Located on the leg and arm. The subject is a male aged 30–39. This image was taken at a distance: 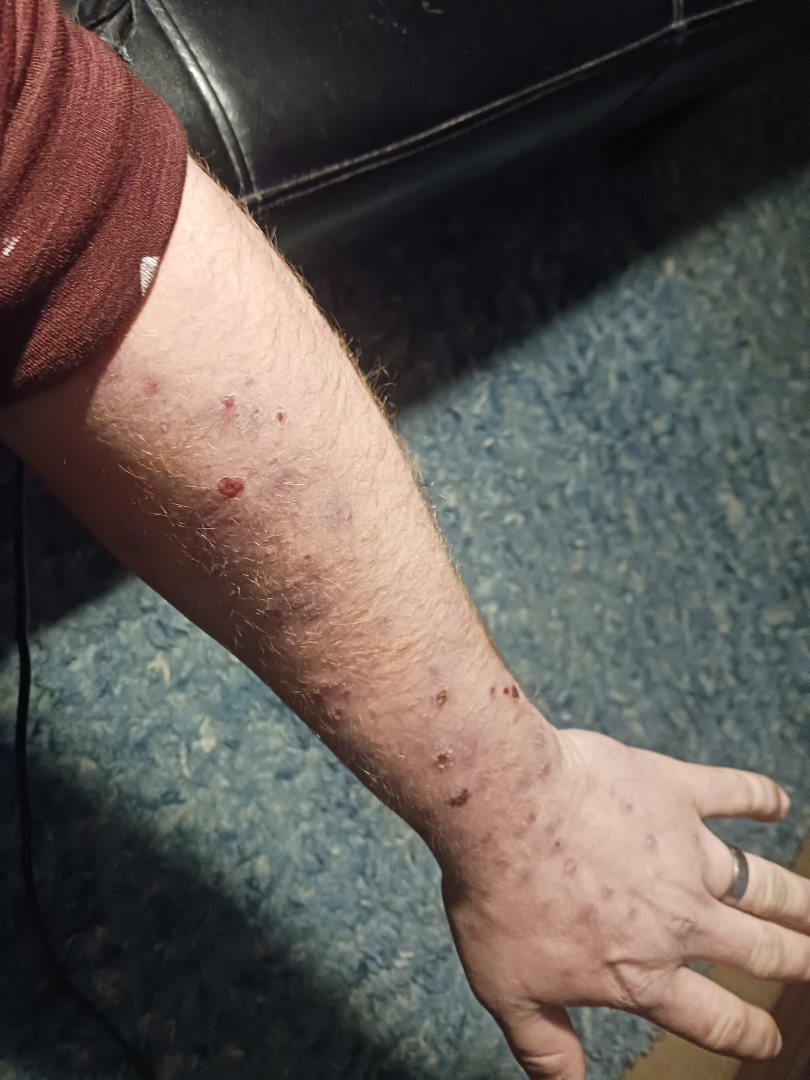Case summary:
* assessment — not assessable
* onset — three to twelve months
* texture — raised or bumpy and fluid-filled
* other reported symptoms — fatigue, mouth sores and joint pain
* patient-reported symptoms — enlargement, bleeding, bothersome appearance and pain